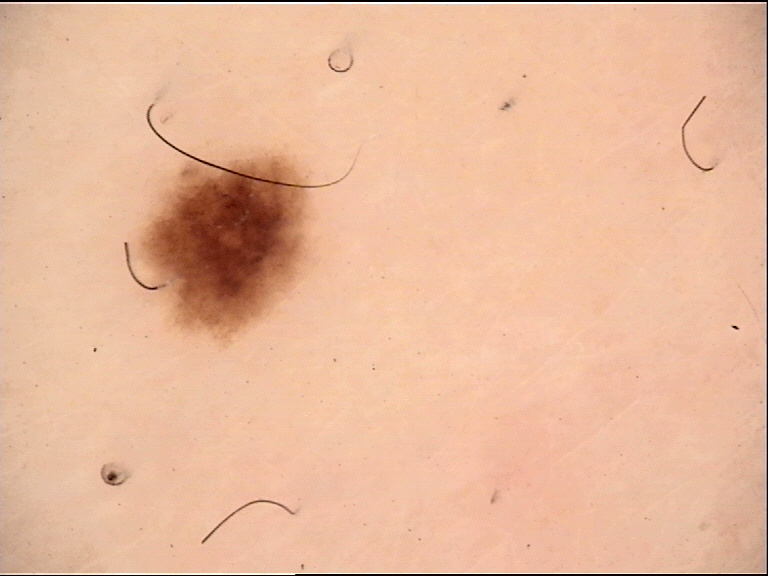Impression:
Consistent with a junctional nevus.